The back of the hand, arm and head or neck are involved · the lesion is described as fluid-filled, raised or bumpy and rough or flaky · the photograph is a close-up of the affected area.
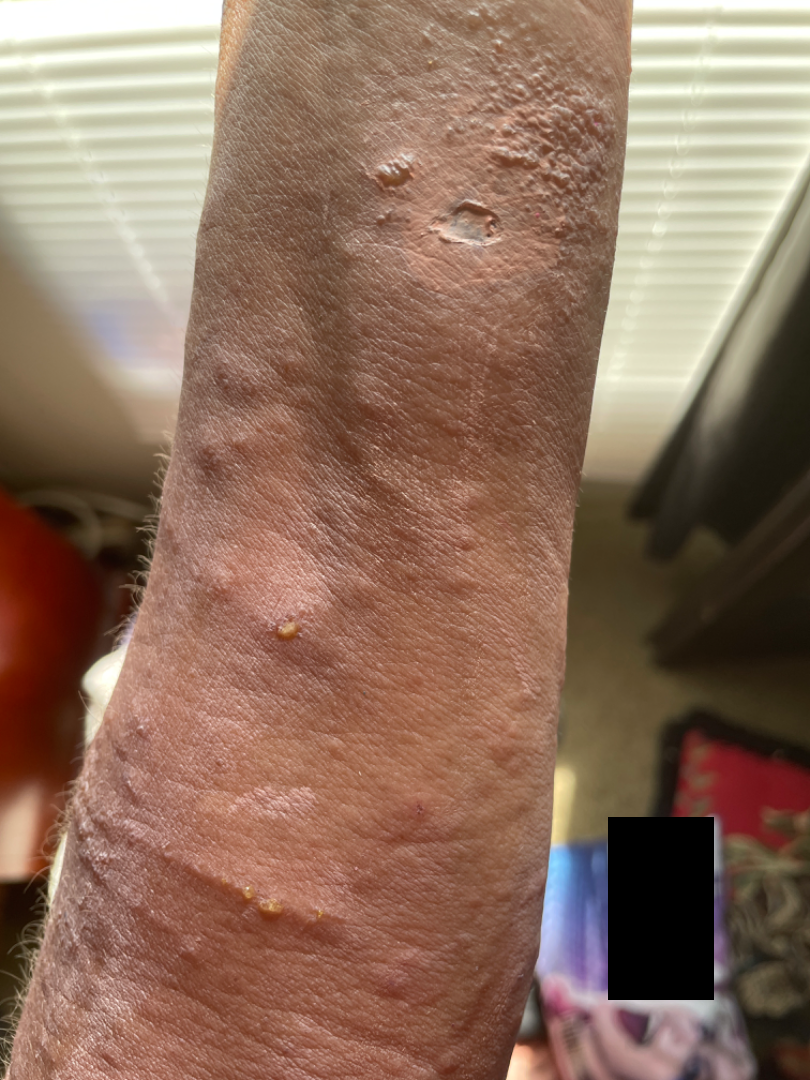On photographic review by a dermatologist, the leading impression is Allergic Contact Dermatitis; possibly Irritant Contact Dermatitis.